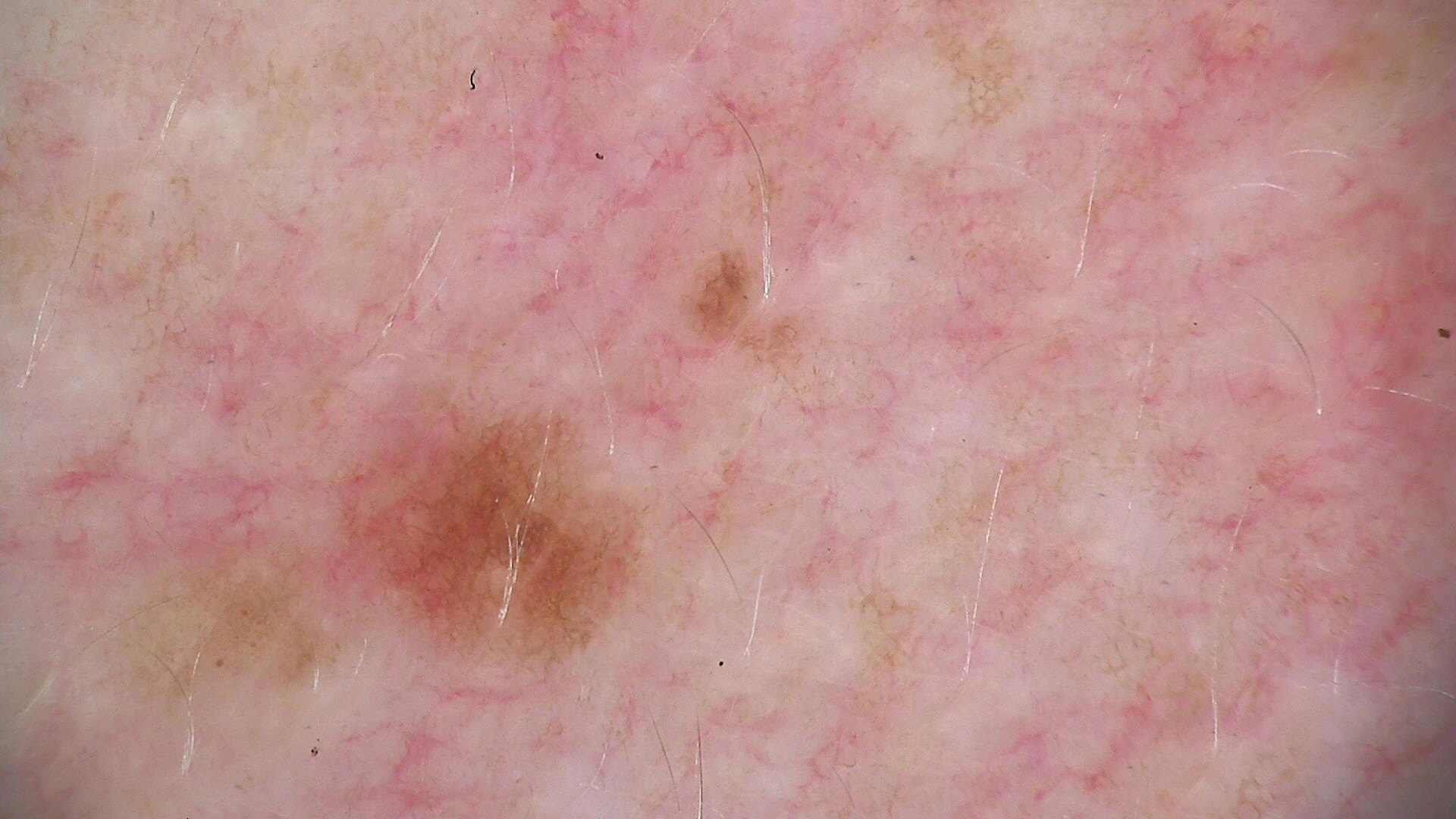A dermoscopic close-up of a skin lesion. Classified as a dysplastic junctional nevus.